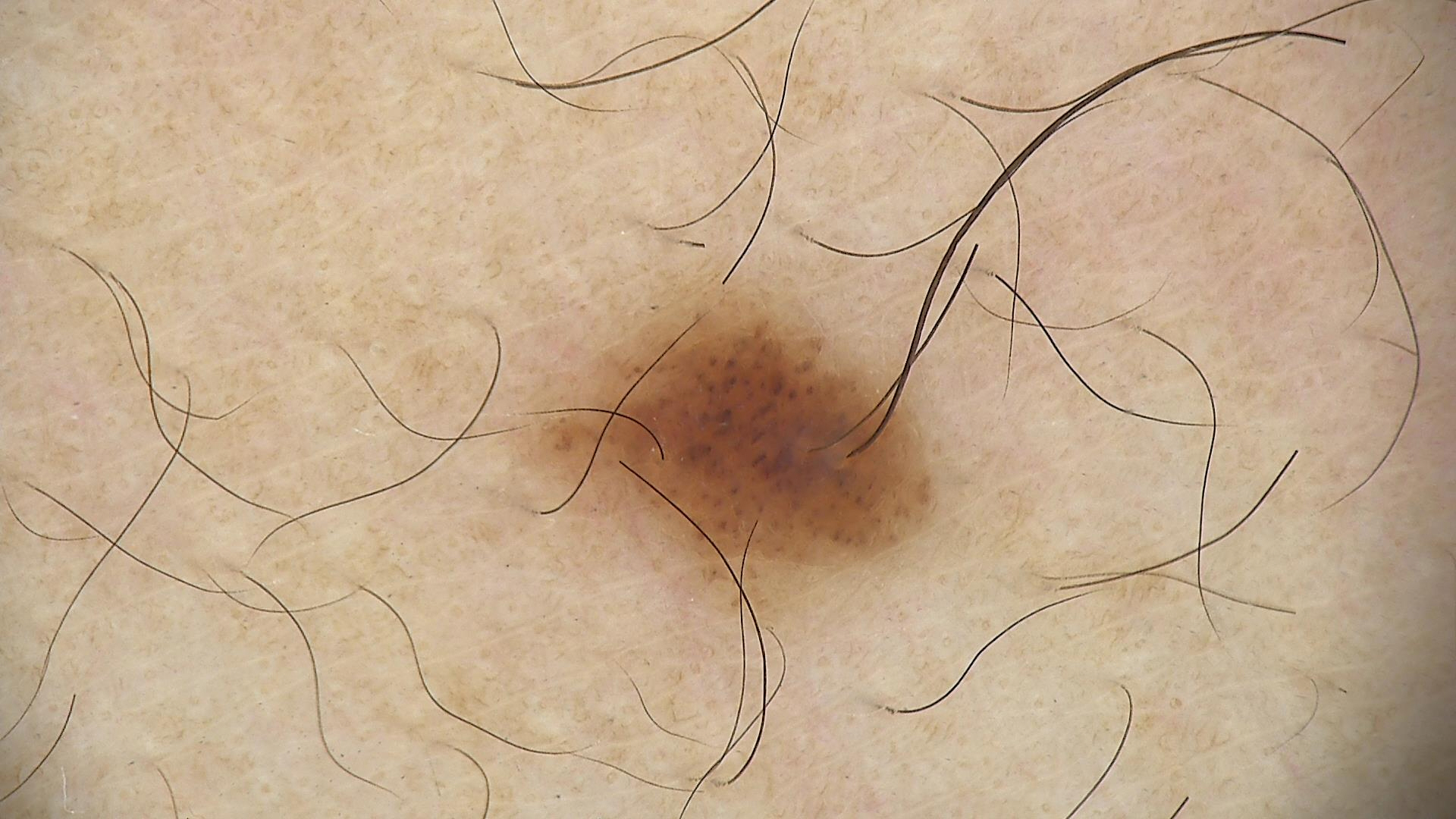  image: dermoscopy
  diagnosis:
    name: compound nevus
    code: cb
    malignancy: benign
    super_class: melanocytic
    confirmation: expert consensus